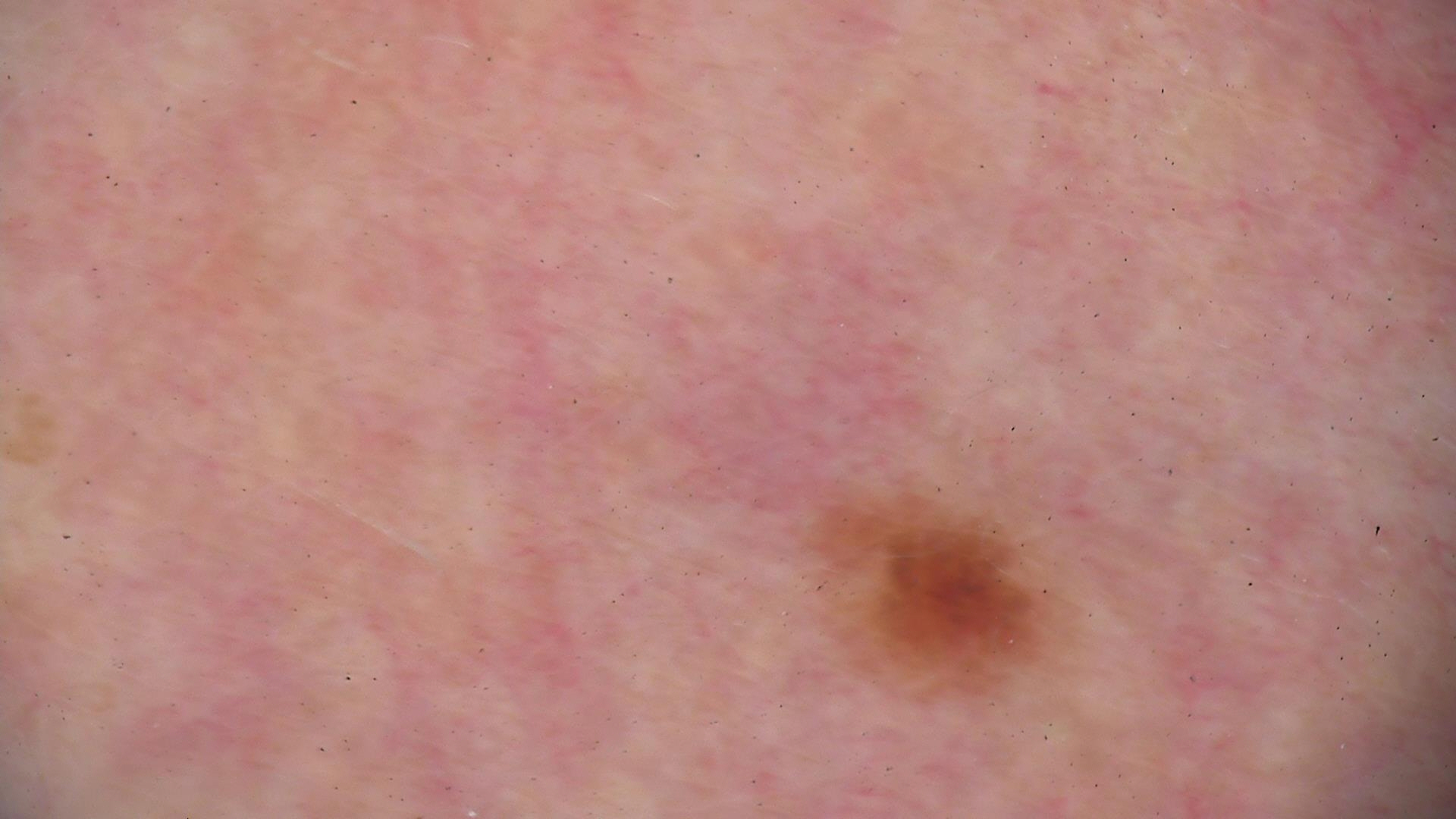label = dysplastic junctional nevus (expert consensus)